Dermoscopy of a skin lesion: 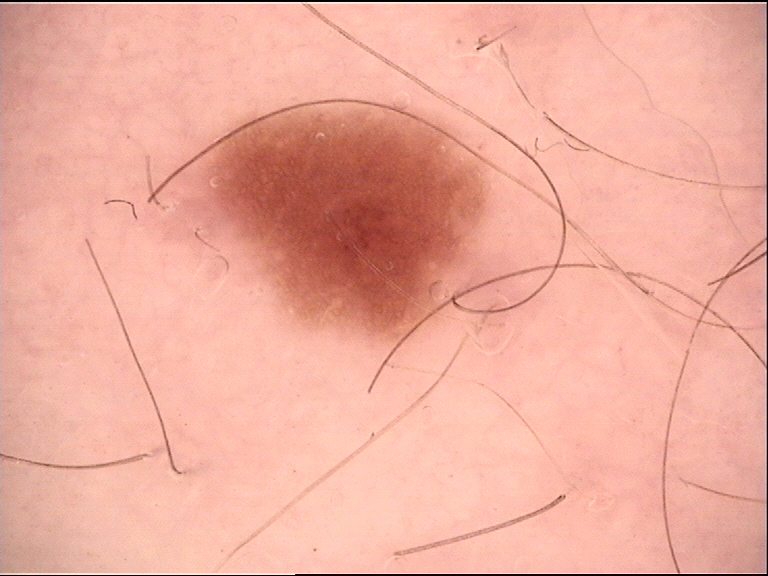The diagnosis was a benign lesion — a dysplastic junctional nevus.